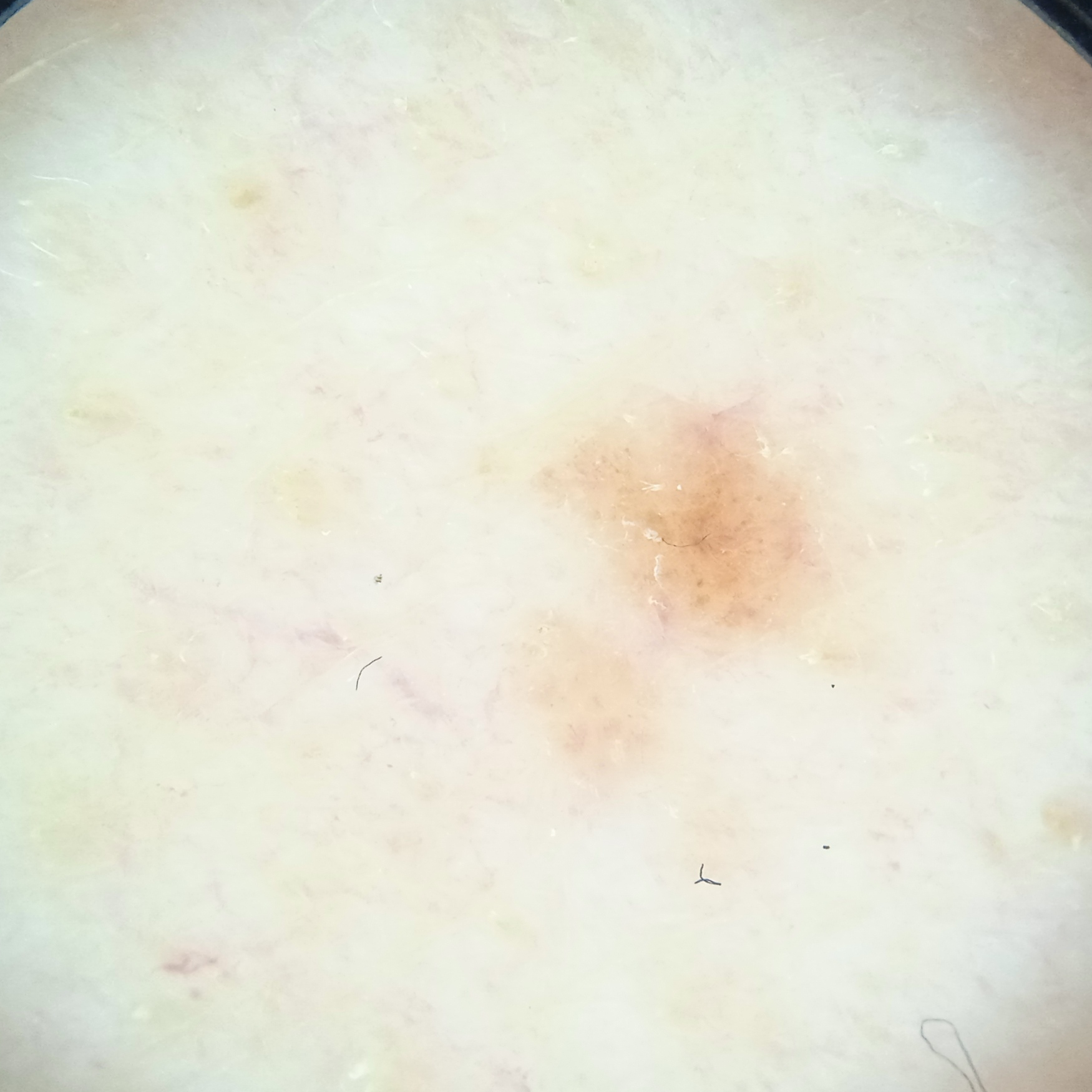Case:
* image: dermatoscopic image
* subject: male, 65 years of age
* nevus count: numerous melanocytic nevi
* sun reaction: skin reddens painfully with sun exposure
* risk factors: a family history of skin cancer, a personal history of skin cancer, immunosuppression
* referral: research study (no referral diagnosis)
* site: the back
* lesion size: 2.8 mm
* assessment: melanocytic nevus (dermatologist consensus)